The contributor is a male aged 18–29 · the lesion involves the front of the torso · an image taken at an angle — 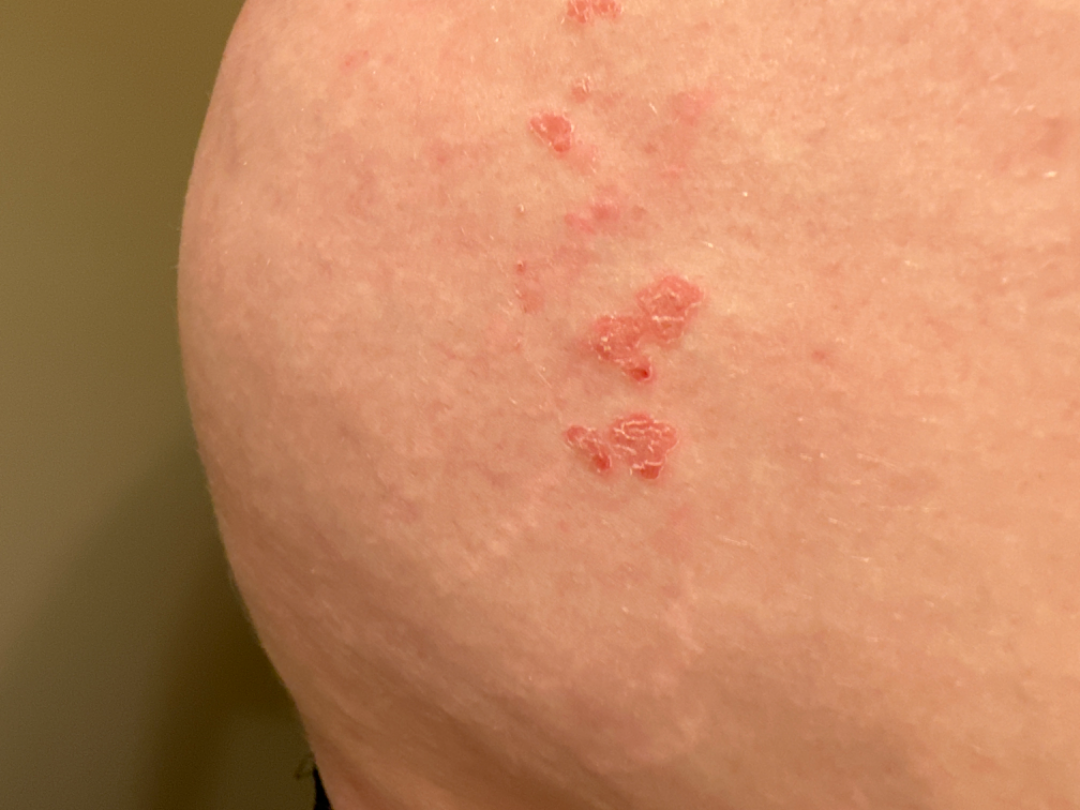The skin condition could not be confidently assessed from this image.